Dermoscopy of a skin lesion. A male subject aged approximately 60.
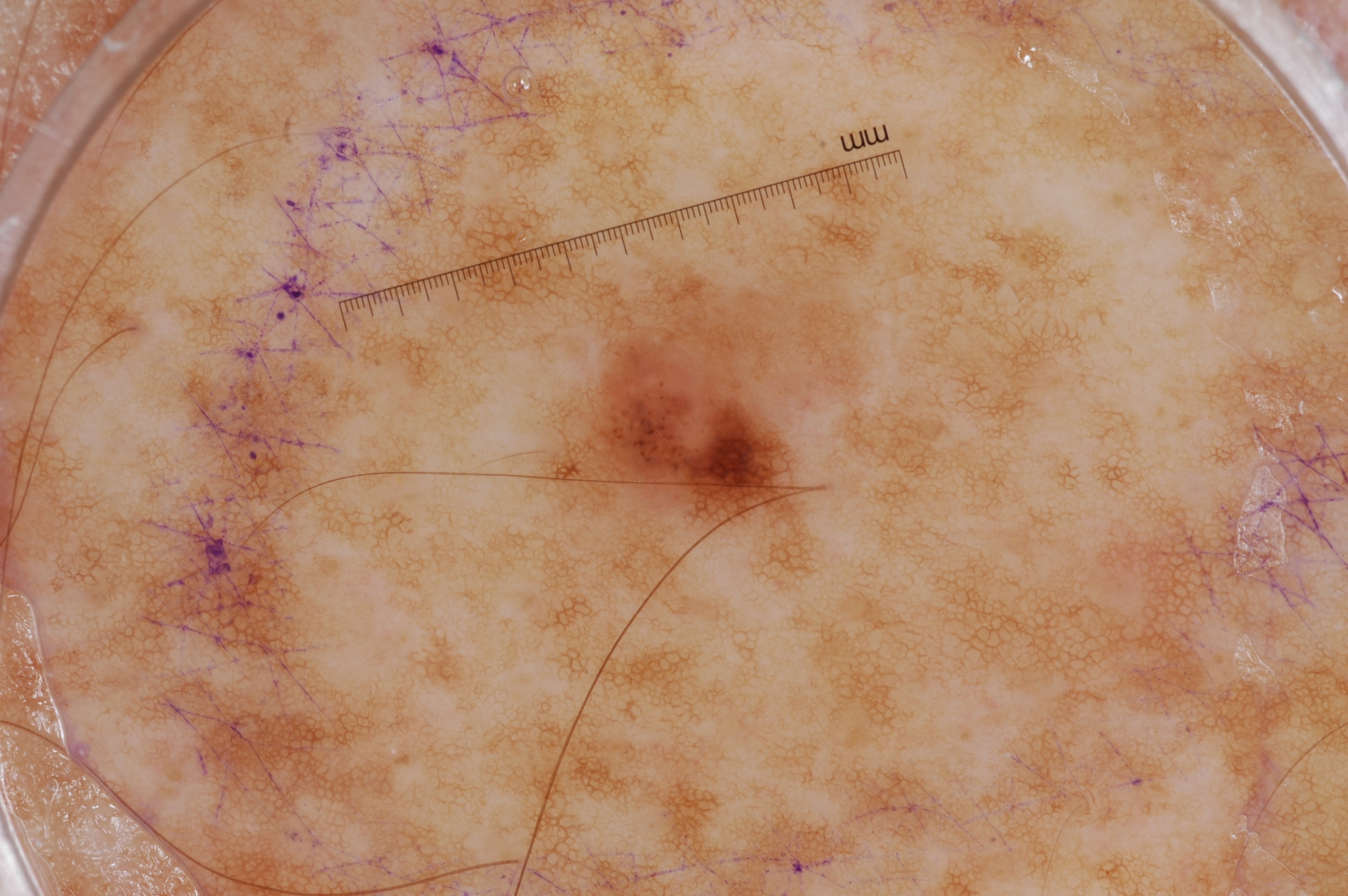Q: How large is the lesion within the image?
A: small
Q: Which dermoscopic features were noted?
A: pigment network
Q: What is the lesion's bounding box?
A: box(537, 266, 863, 539)
Q: What is the diagnosis?
A: a melanocytic nevus, a benign skin lesion